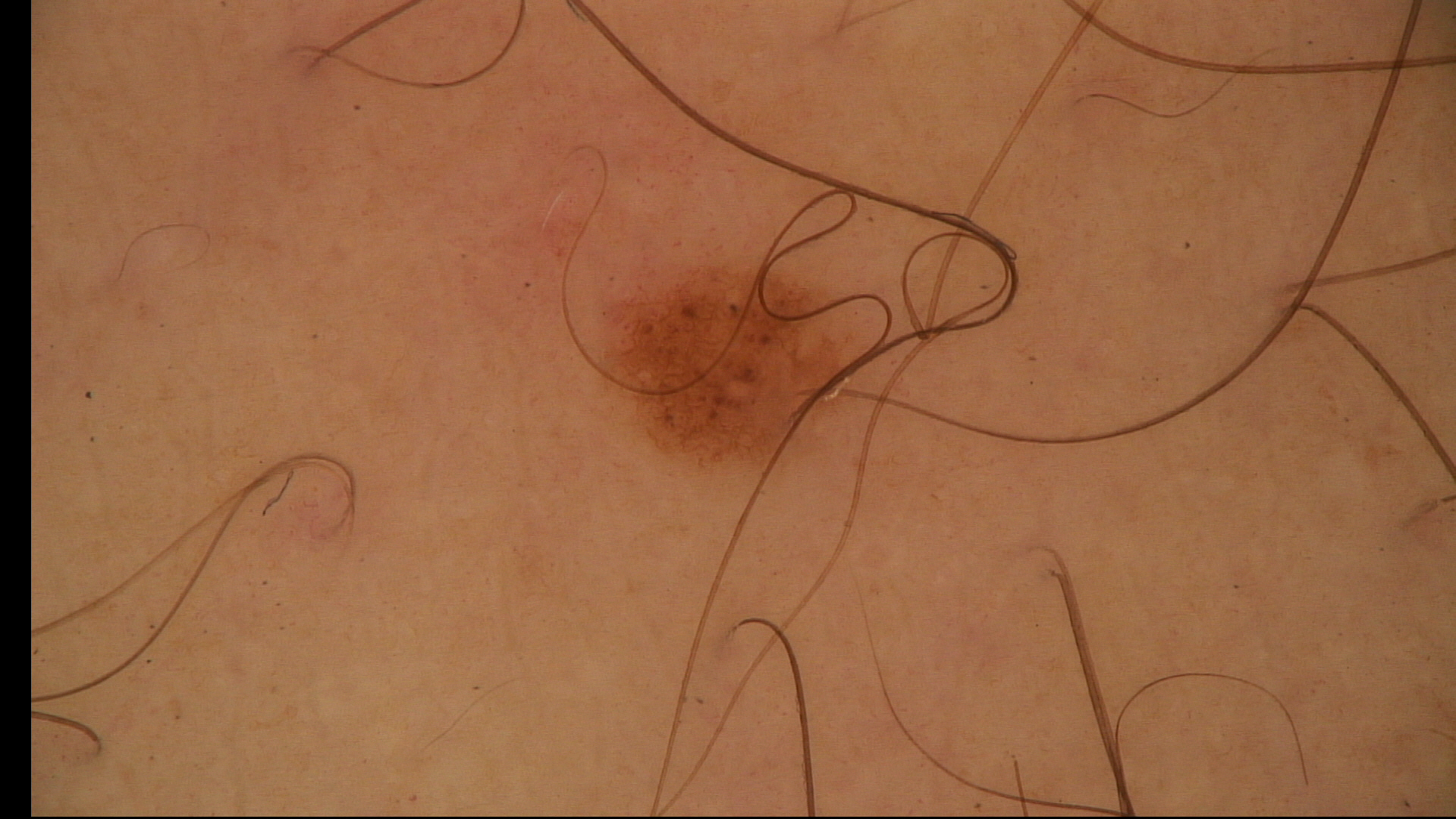Findings:
* image type — dermatoscopy
* classification — banal
* assessment — junctional nevus (expert consensus)